A dermatoscopic image of a skin lesion:
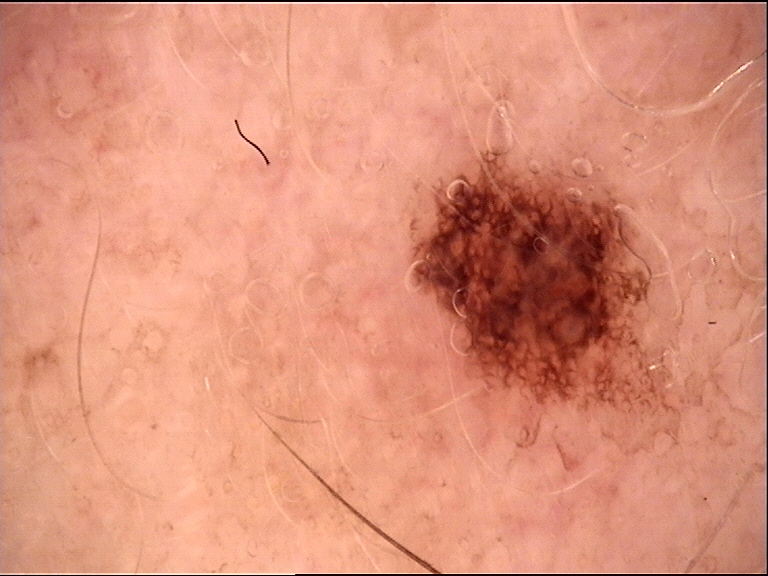assessment = dysplastic junctional nevus (expert consensus).